This is a close-up image · the lesion involves the leg · symptoms reported: itching · present for less than one week · no relevant systemic symptoms.
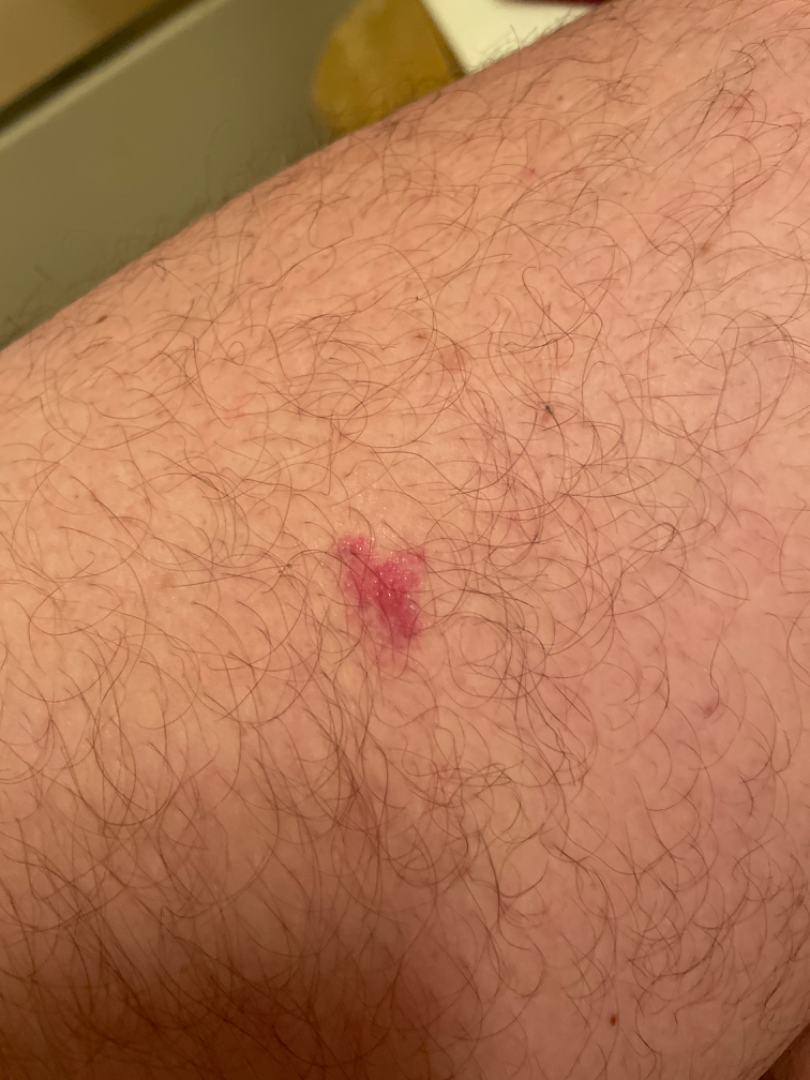On remote review of the image, Allergic Contact Dermatitis (weight 0.50); Basal Cell Carcinoma (weight 0.50).